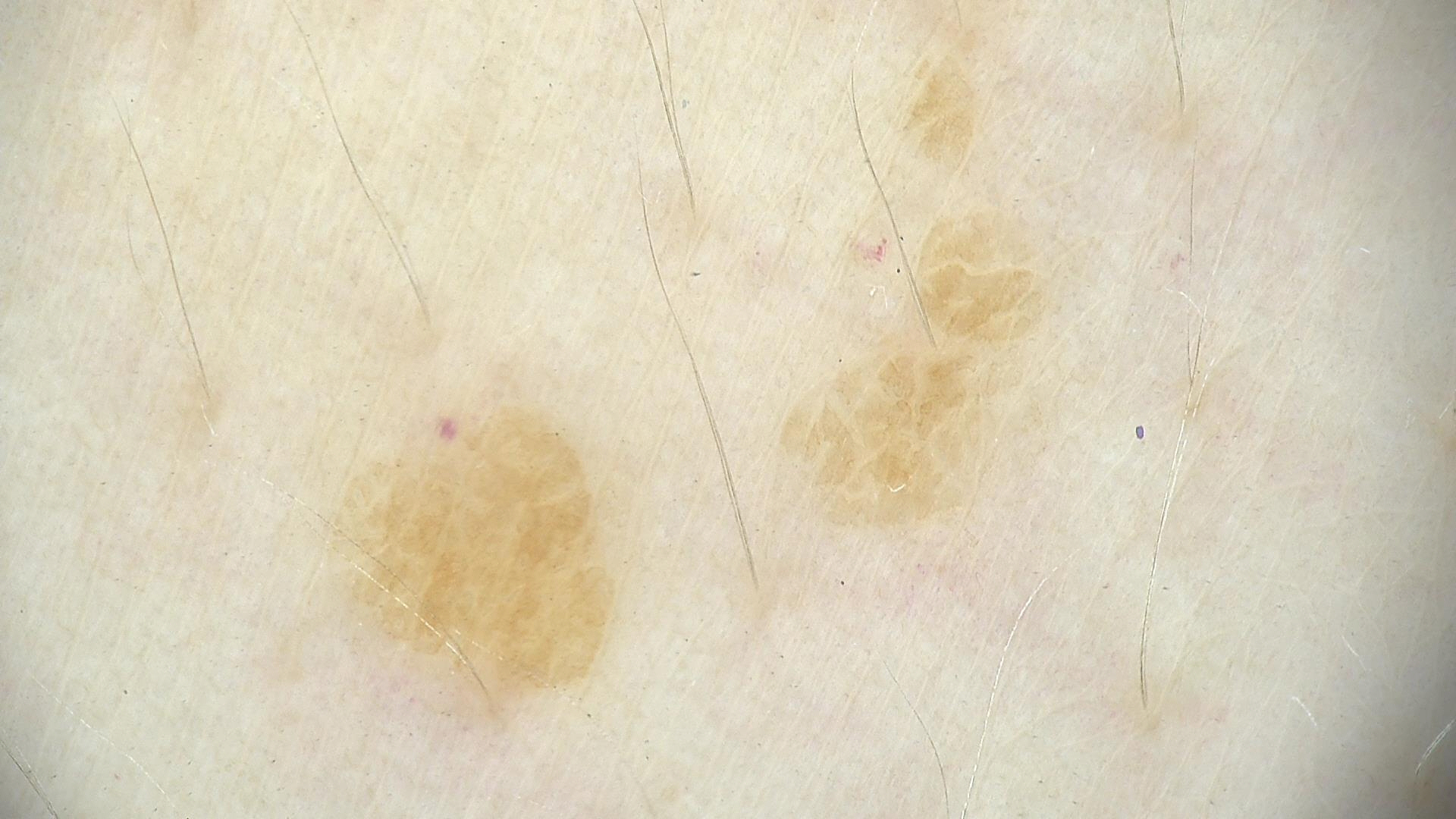Q: What is this lesion?
A: seborrheic keratosis (expert consensus)